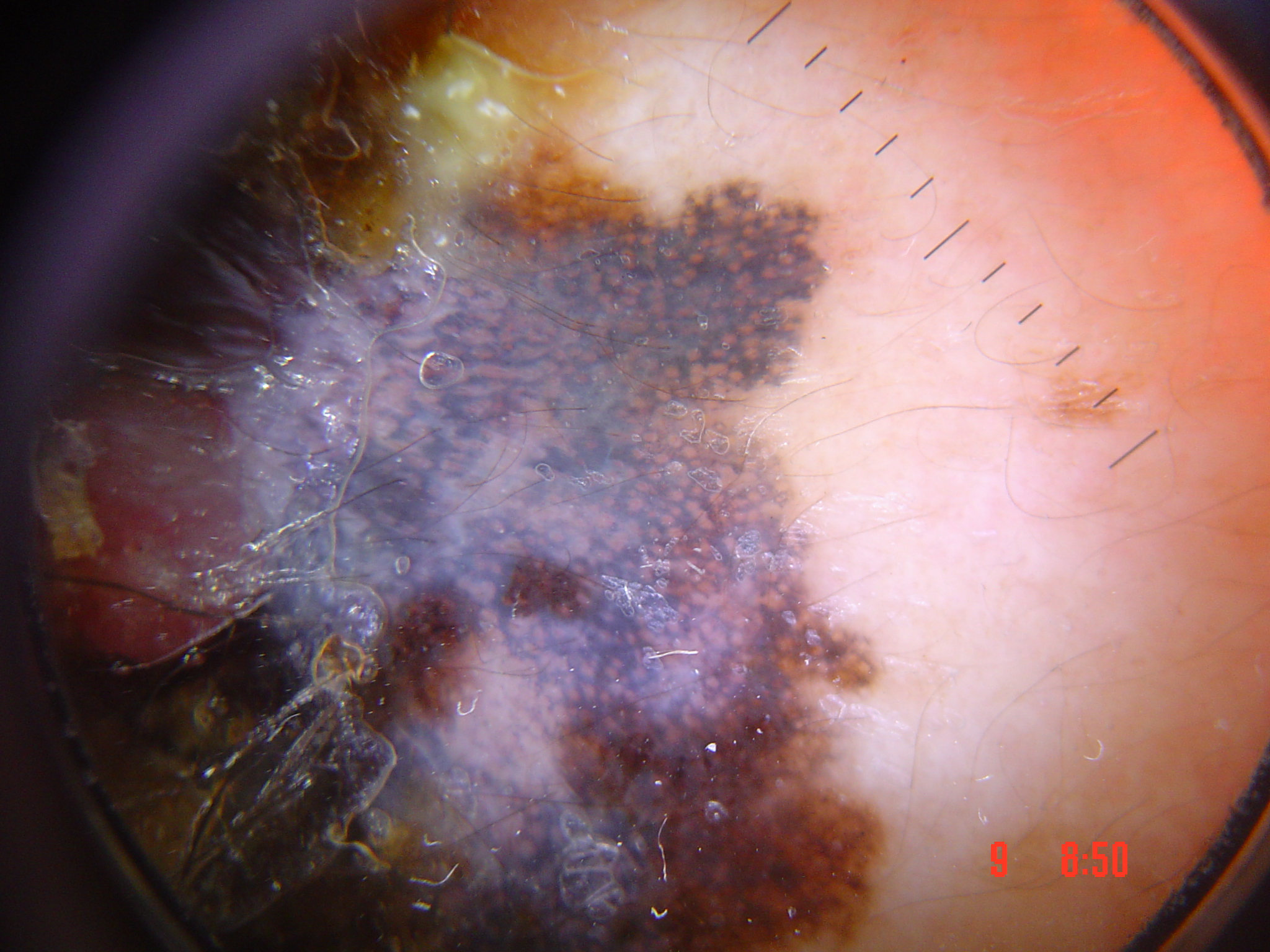imaging — dermatoscopy
diagnostic label — lentigo maligna melanoma (biopsy-proven)